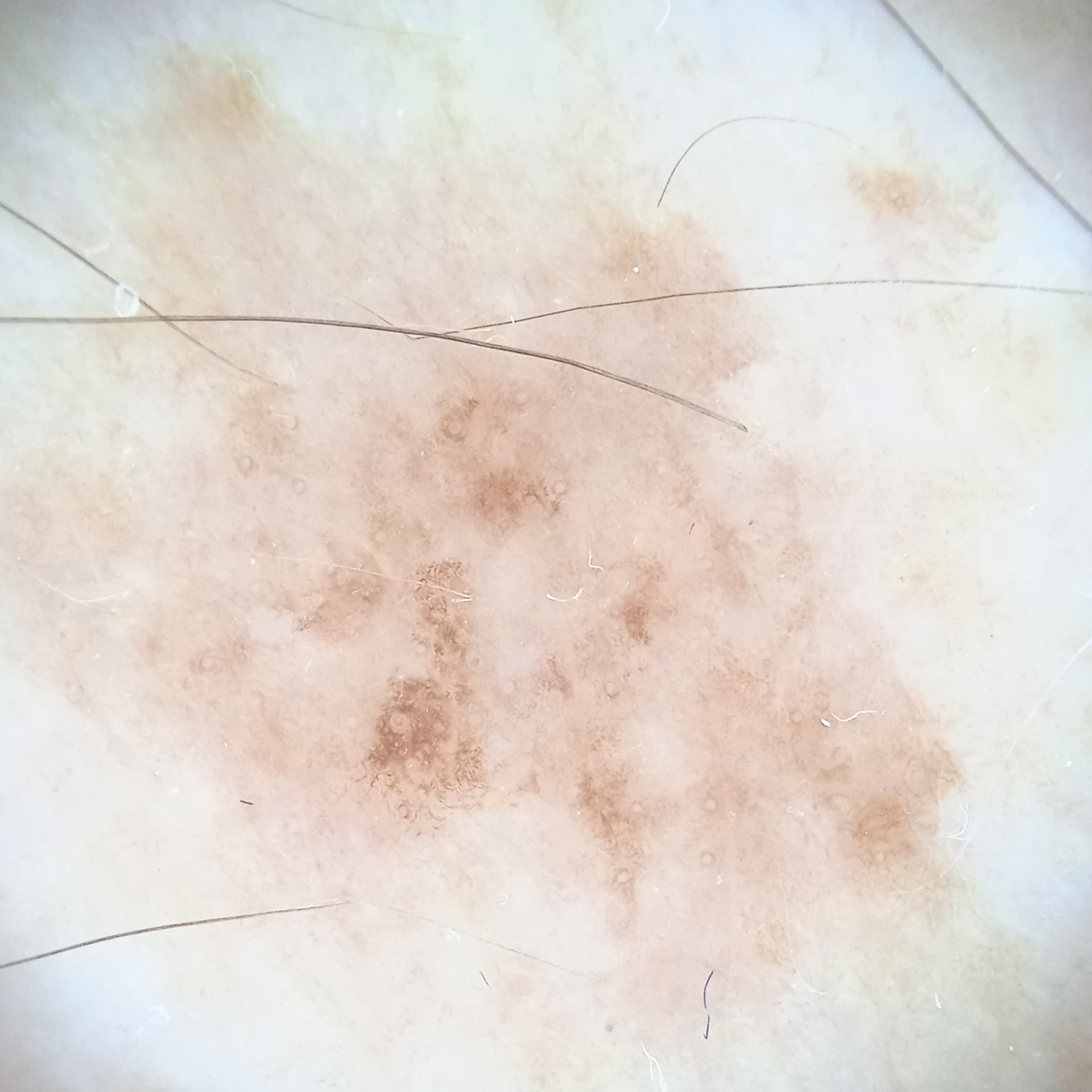The diagnostic impression was a melanoma.